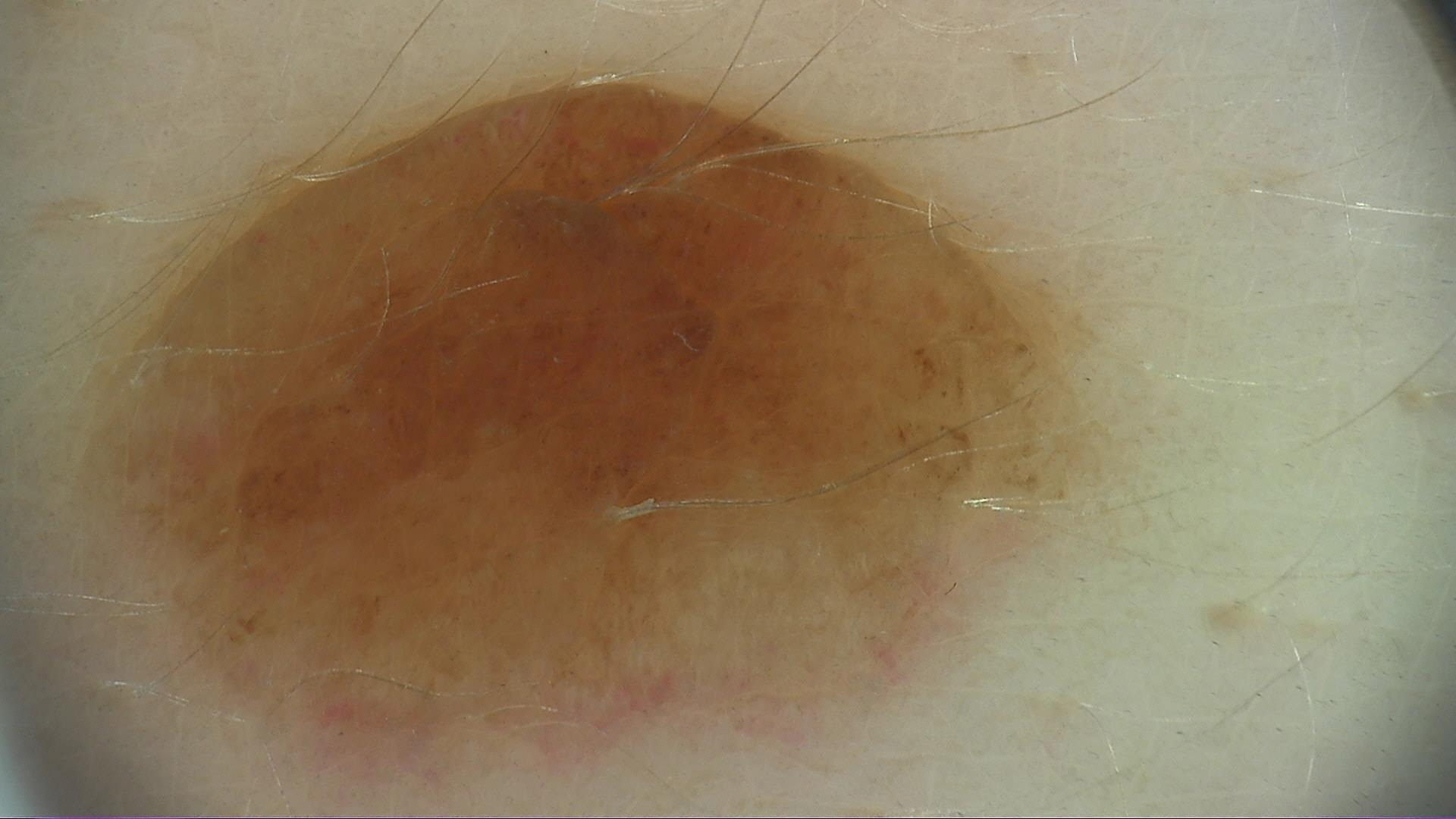Conclusion: Labeled as a compound nevus.